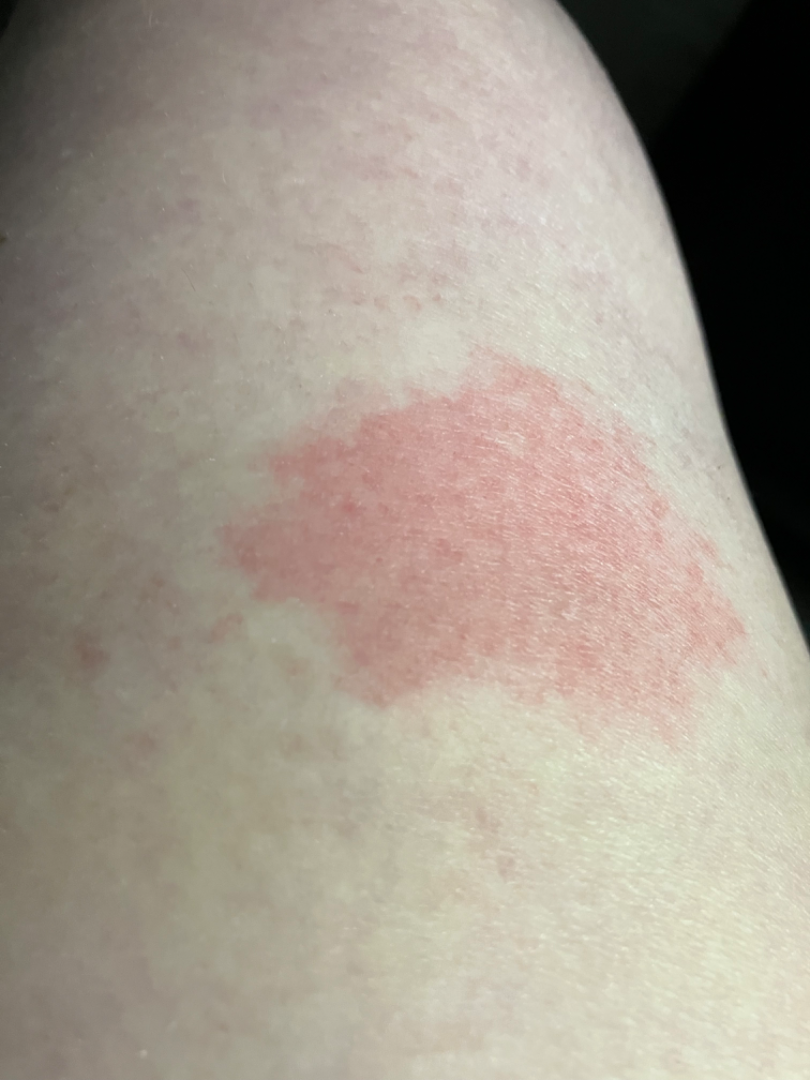Findings:
– patient-reported symptoms — bothersome appearance
– patient's own categorization — skin that appeared healthy to them
– affected area — leg
– history — less than one week
– shot type — close-up
– constitutional symptoms — none reported
– impression — Allergic Contact Dermatitis and Erythema migrans were each considered, in no particular order